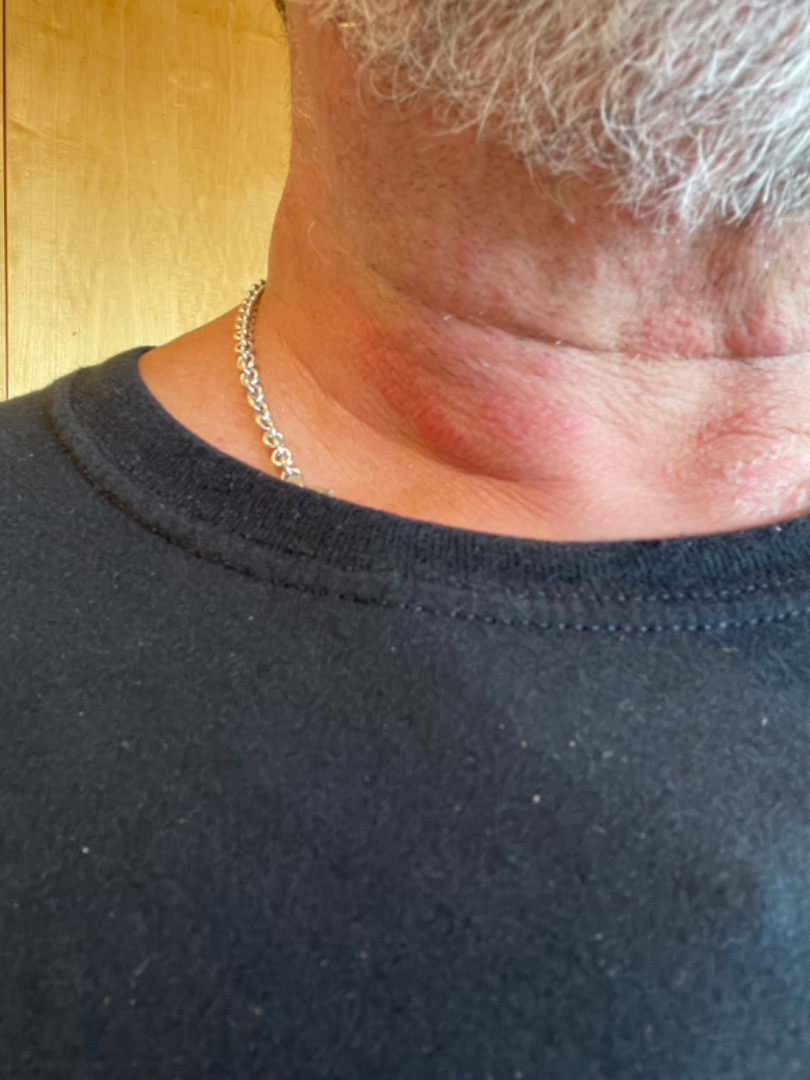History:
The lesion is associated with itching and bothersome appearance. The patient indicates the lesion is rough or flaky. An image taken at an angle. The condition has been present for less than one week. The patient is male. Skin tone: Fitzpatrick II; human graders estimated a Monk skin tone scale of 2. The affected area is the head or neck.
Impression:
Allergic Contact Dermatitis (leading); Contact dermatitis, NOS (unlikely); Eczema (unlikely); Tinea (unlikely); Irritant Contact Dermatitis (unlikely); Photodermatitis (unlikely).